A skin lesion imaged with a dermatoscope.
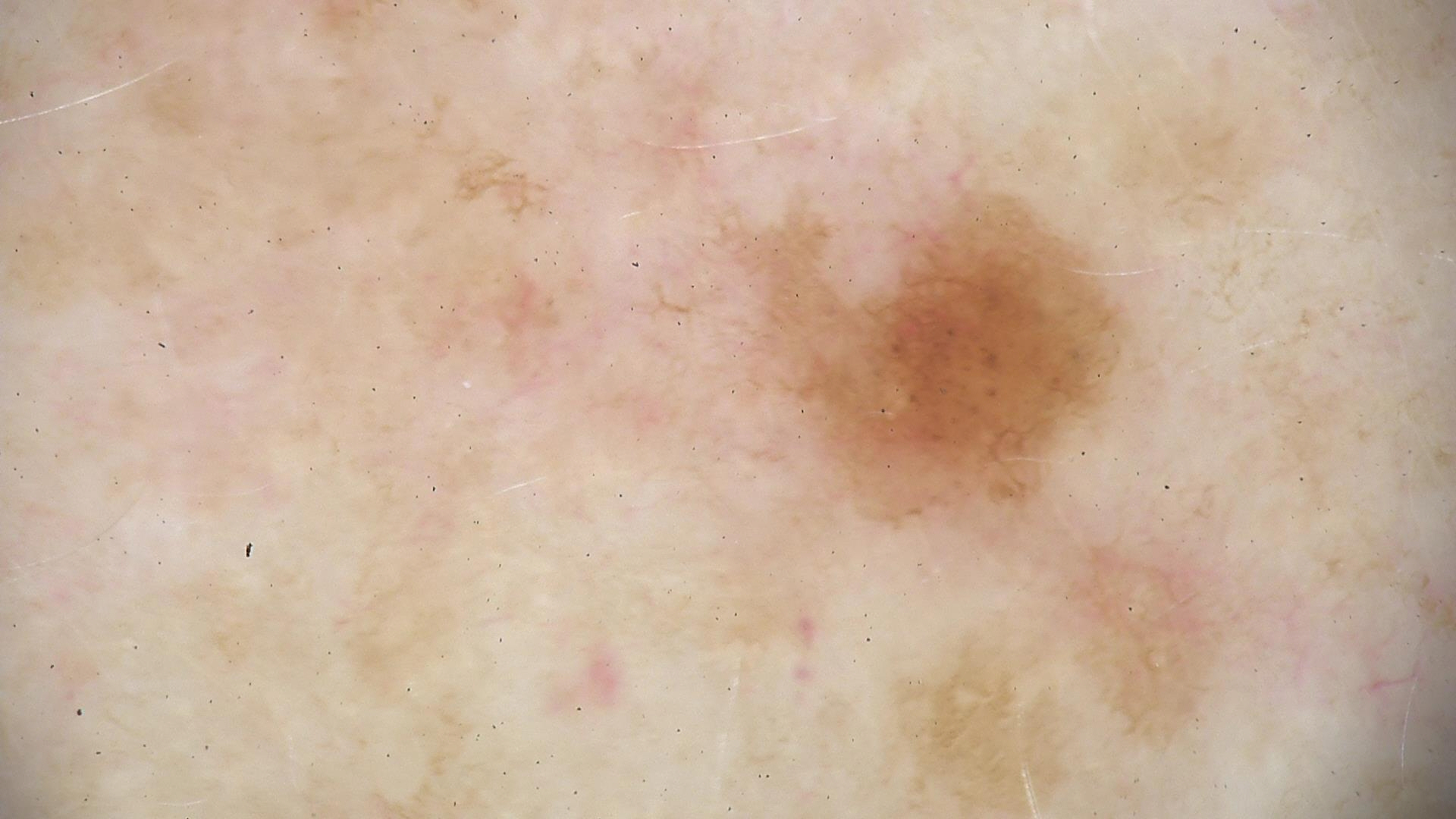Labeled as a dysplastic junctional nevus.